The photograph was taken at an angle; male contributor, age 18–29; the lesion involves the leg — 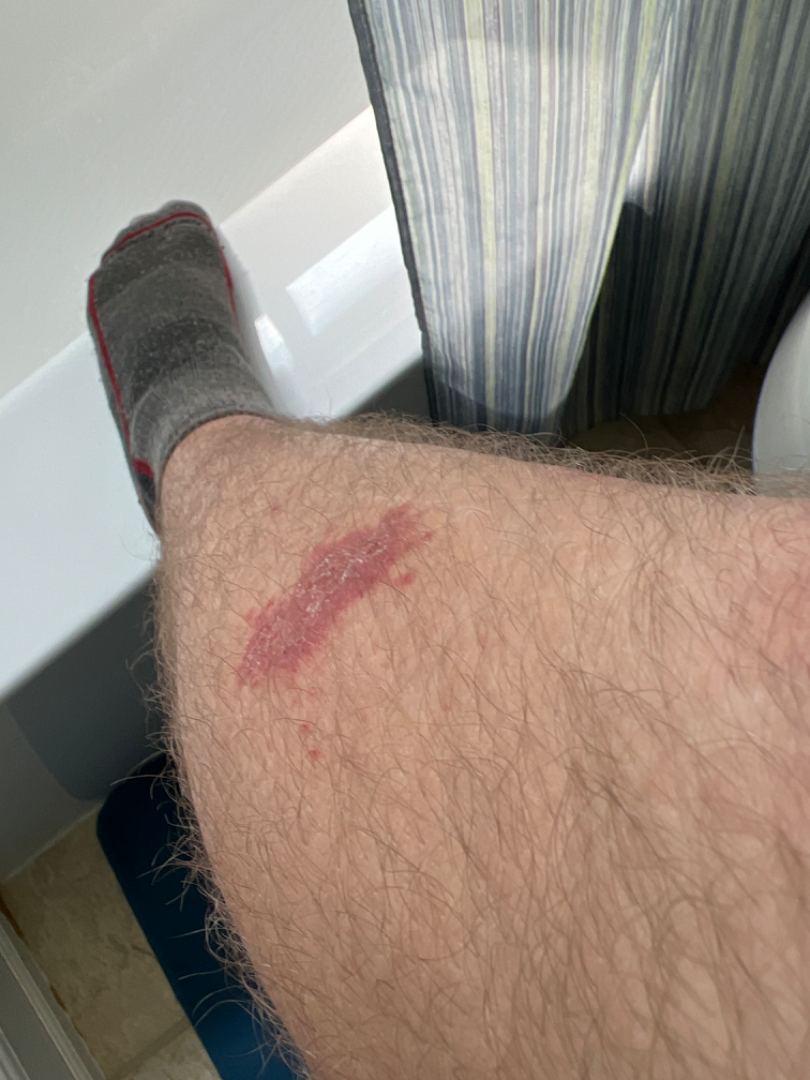assessment: not assessable